The lesion is described as raised or bumpy. Close-up view. The subject is 40–49, female. The patient reports bothersome appearance, burning and itching. The patient described the issue as skin that appeared healthy to them. The patient reports the condition has been present for less than one week. Located on the arm. Skin tone: Fitzpatrick phototype I.
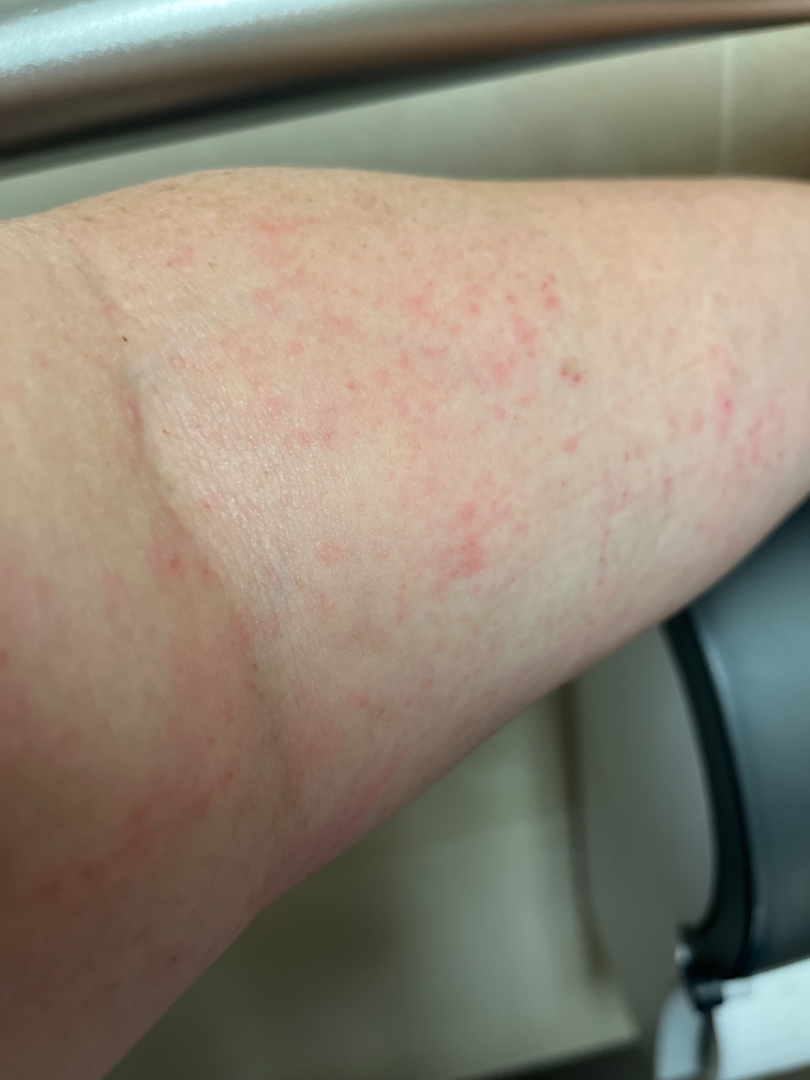{"differential": {"tied_lead": ["Acute dermatitis, NOS", "Irritant Contact Dermatitis"], "considered": ["Eczema", "Allergic Contact Dermatitis"]}}